A dermoscopic image of a skin lesion: 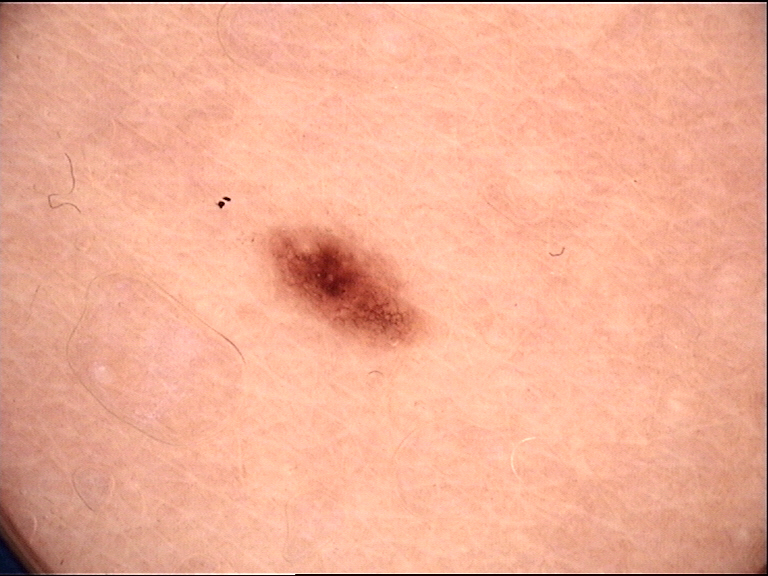Labeled as a benign lesion — a dysplastic junctional nevus.